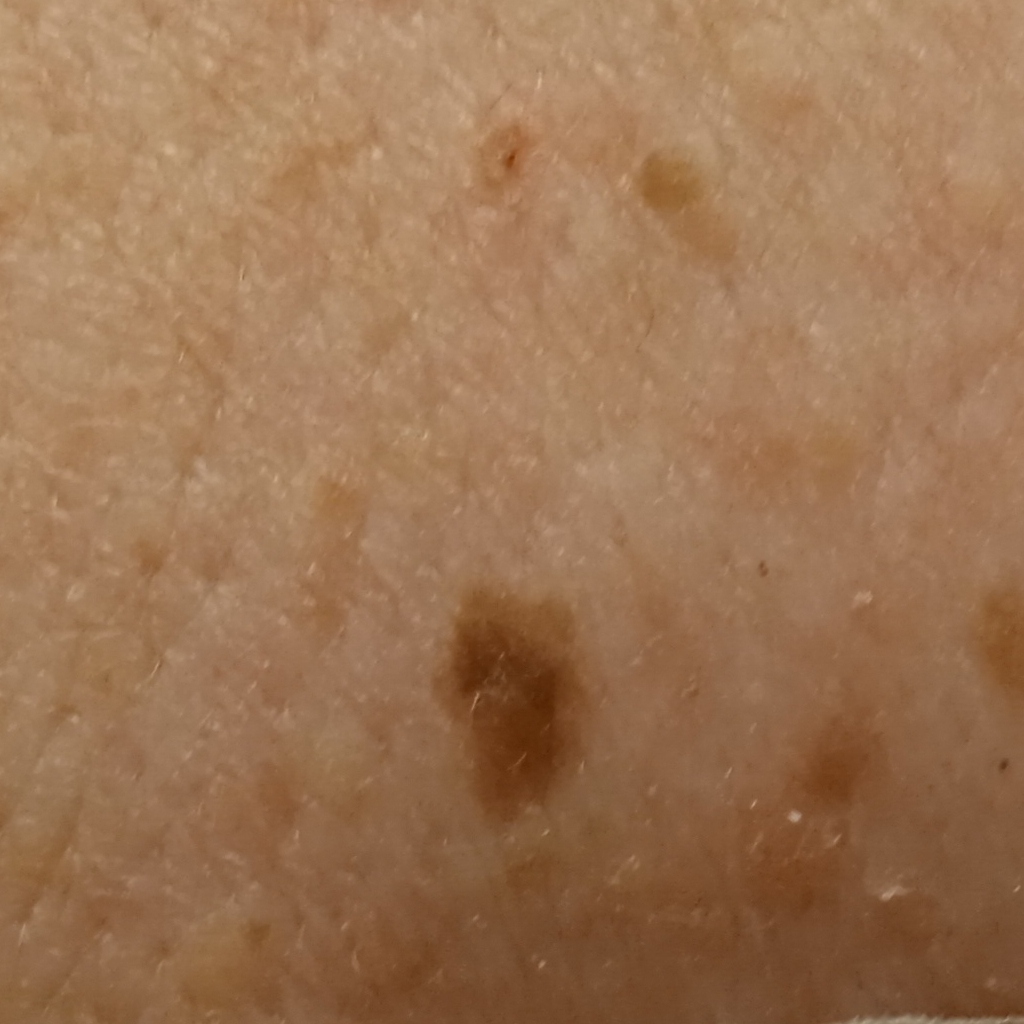Q: Why was this imaged?
A: research study (no referral diagnosis)
Q: What kind of image is this?
A: clinical photo
Q: Tell me about the patient.
A: female, age 55
Q: What is the anatomic site?
A: the back
Q: How large is the lesion?
A: 6.3 mm
Q: What was the diagnosis?
A: melanocytic nevus (dermatologist consensus)